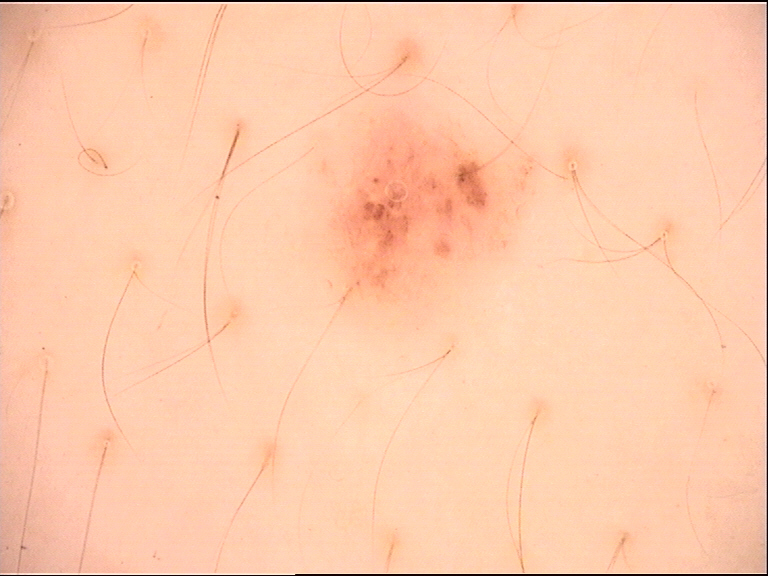label=compound nevus (expert consensus)